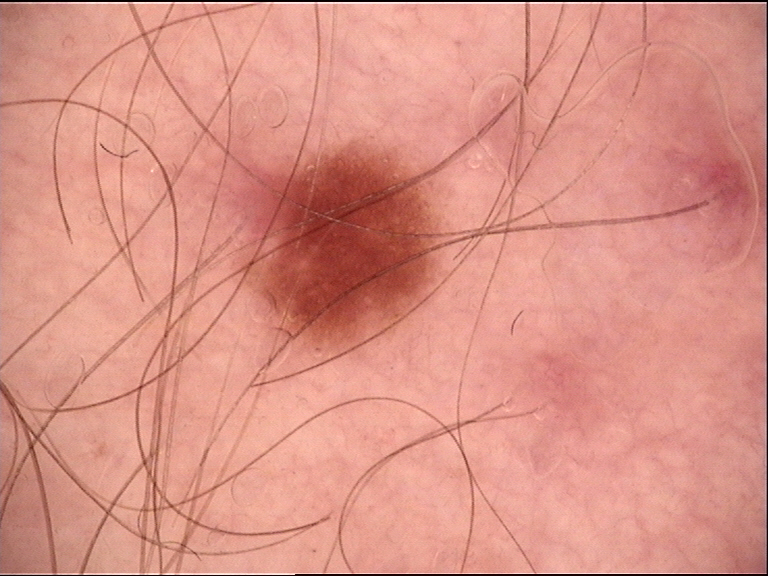Q: What is the imaging modality?
A: dermatoscopy
Q: What is this lesion?
A: dysplastic junctional nevus (expert consensus)